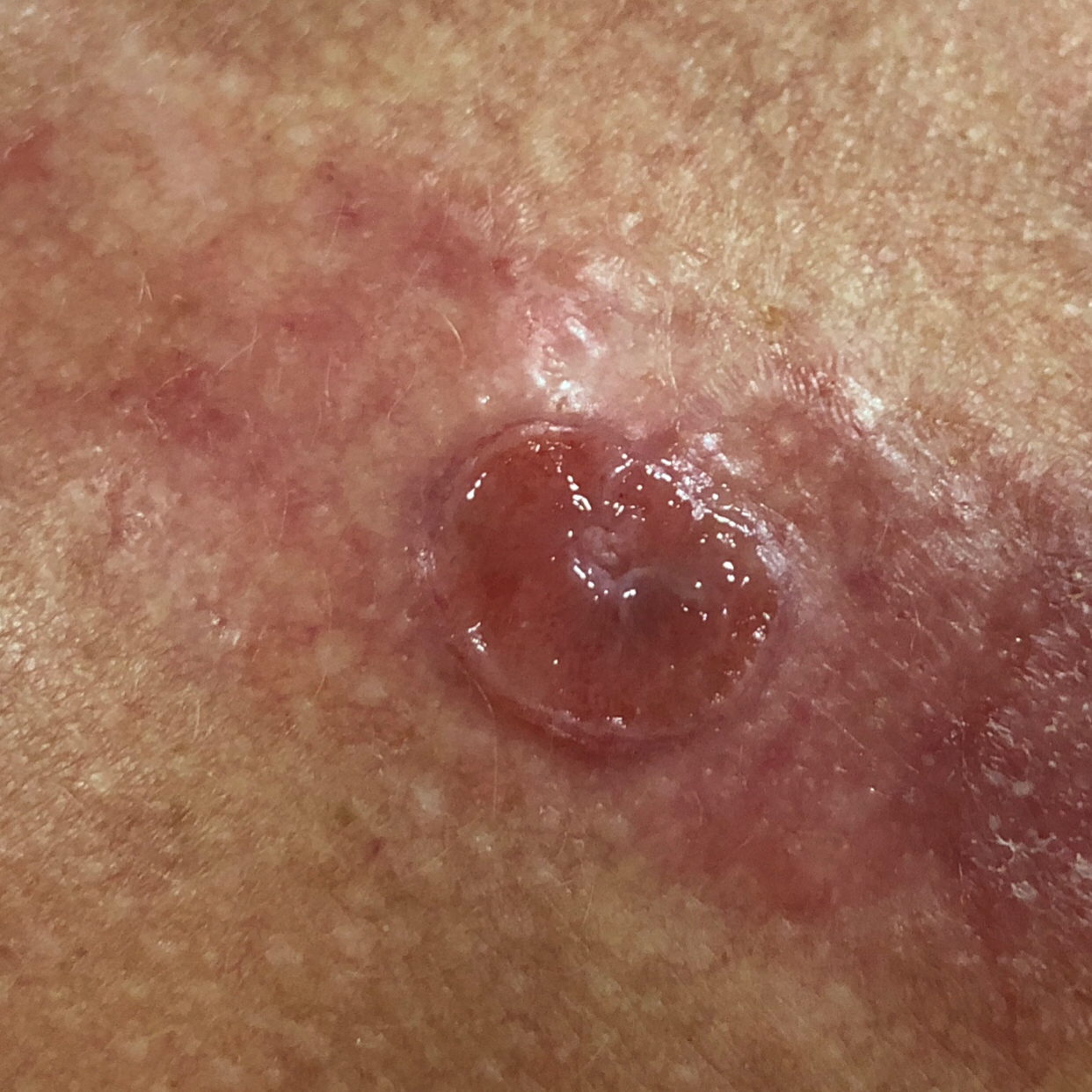Case summary:
Recorded as Fitzpatrick II. A smartphone photograph of a skin lesion. A male subject 68 years old. The chart records prior malignancy (patient or family). The lesion involves the back. Measuring about 15 × 10 mm. The patient describes that the lesion has bled, hurts, and itches, but has not grown and has not changed.
Pathology:
The biopsy diagnosis was a basal cell carcinoma.